A close-up photograph, the patient considered this a rash, skin tone: Fitzpatrick phototype III; human graders estimated Monk skin tone scale 2, the affected area is the back of the torso, the contributor notes the condition has been present for less than one week: 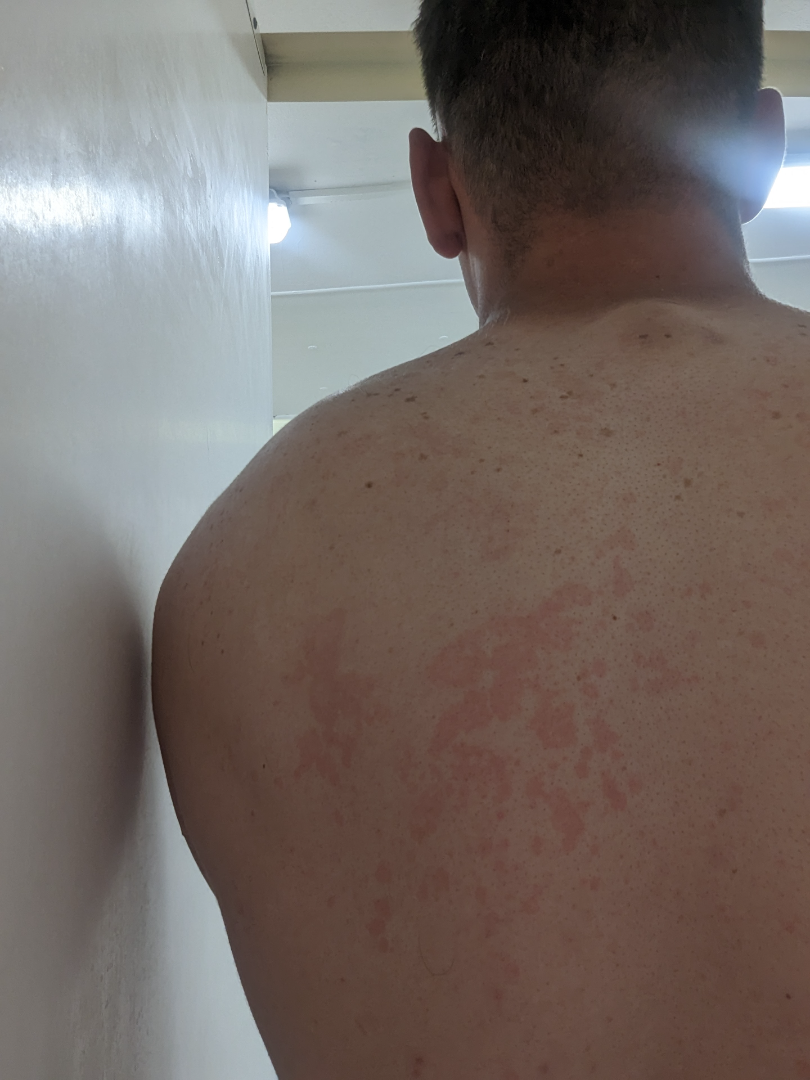The dermatologist could not determine a likely condition from the photograph alone.